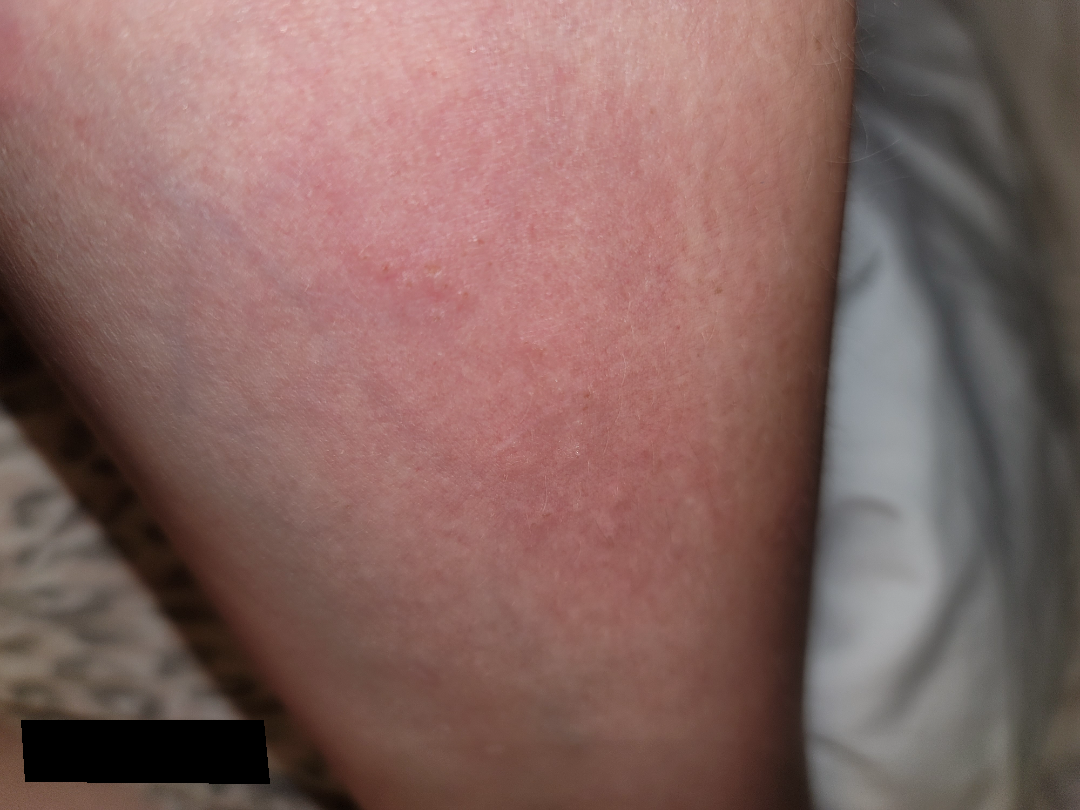<summary>
  <assessment>ungradable on photographic review</assessment>
</summary>